An image taken at a distance · the subject is a female aged 18–29 · the affected area is the arm: 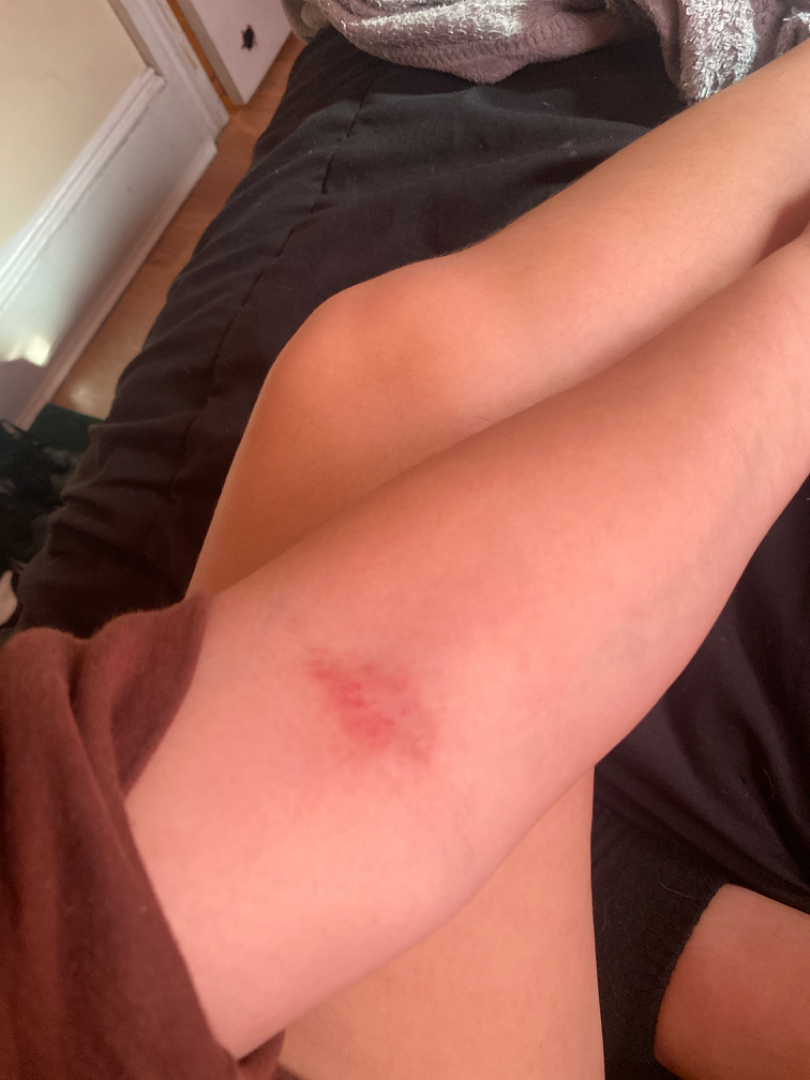Assessment: The leading consideration is Allergic Contact Dermatitis; also consider Abrasion, scrape, or scab; also raised was Eczema.